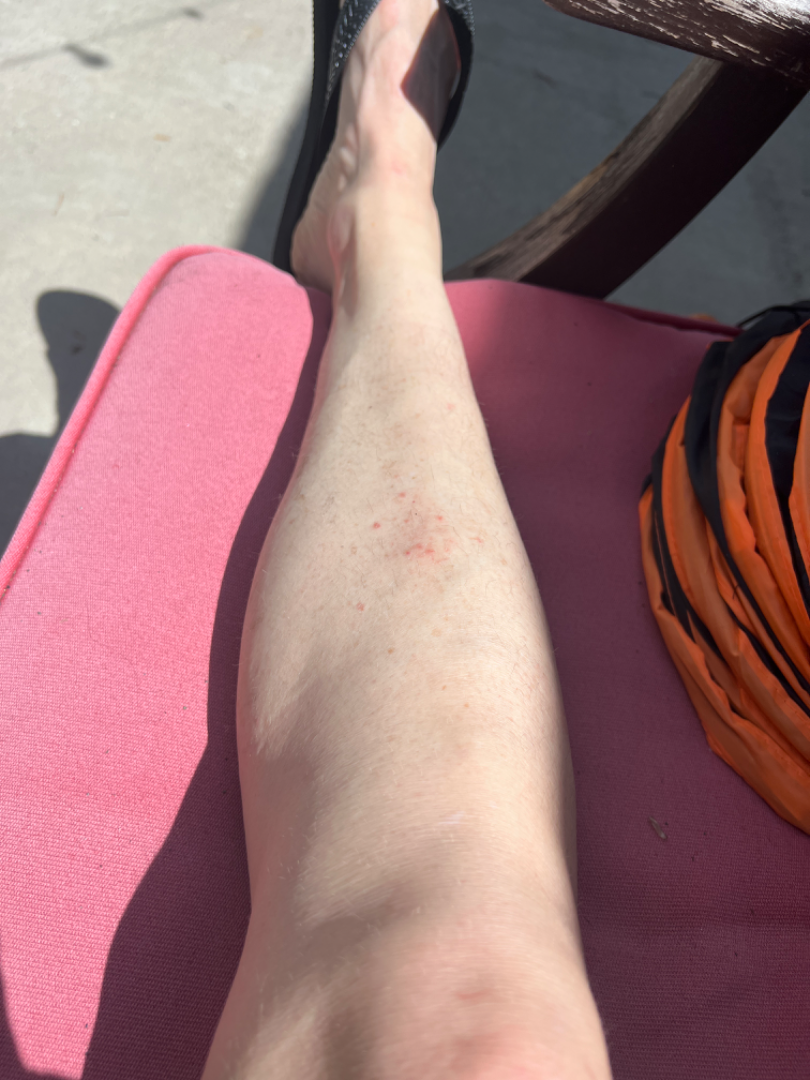<case>
  <differential>
    <tied_lead>Eczema, Stasis Dermatitis</tied_lead>
    <unlikely>Folliculitis</unlikely>
  </differential>
</case>